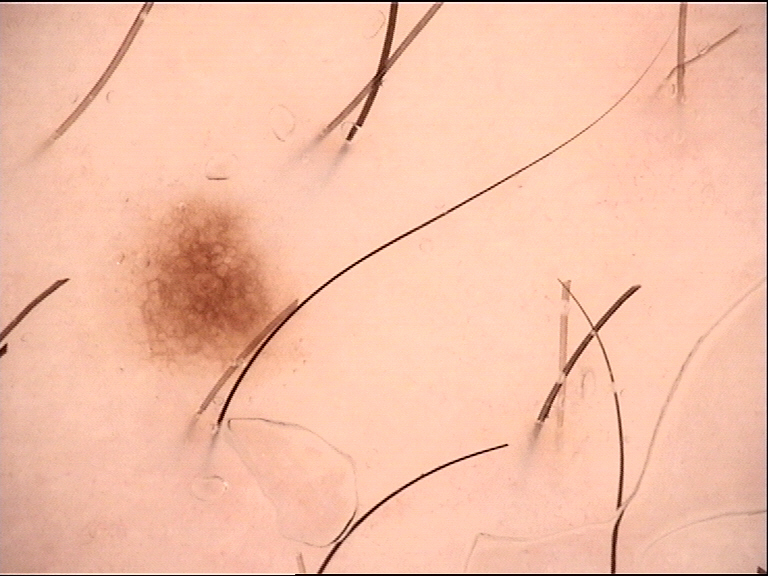diagnostic label: dysplastic junctional nevus (expert consensus).